A clinical photo of a skin lesion taken with a smartphone. The chart notes prior malignancy (patient or family), no tobacco use, and no pesticide exposure. The patient was assessed as skin type I.
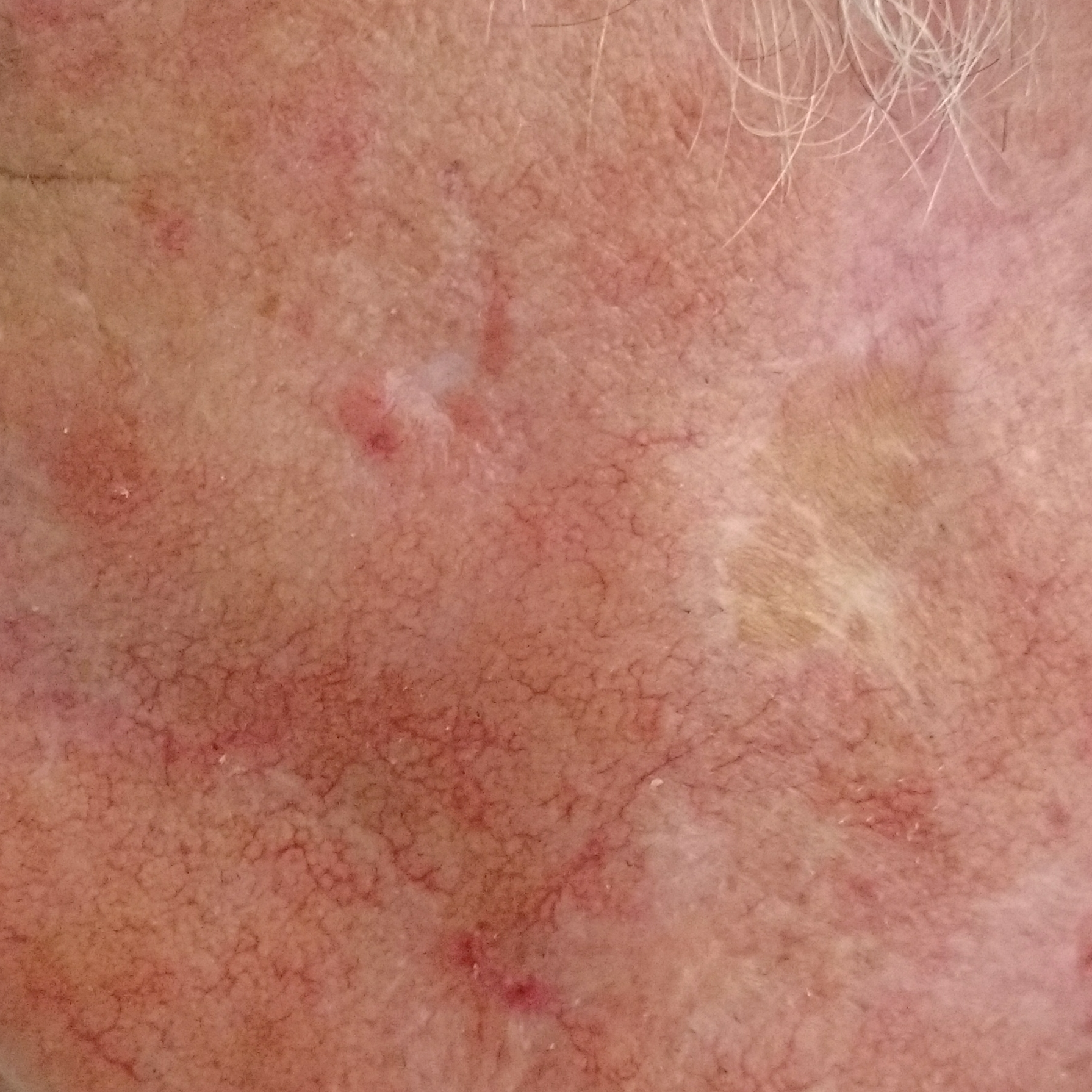size — 11 × 10 mm; pathology — basal cell carcinoma (biopsy-proven).